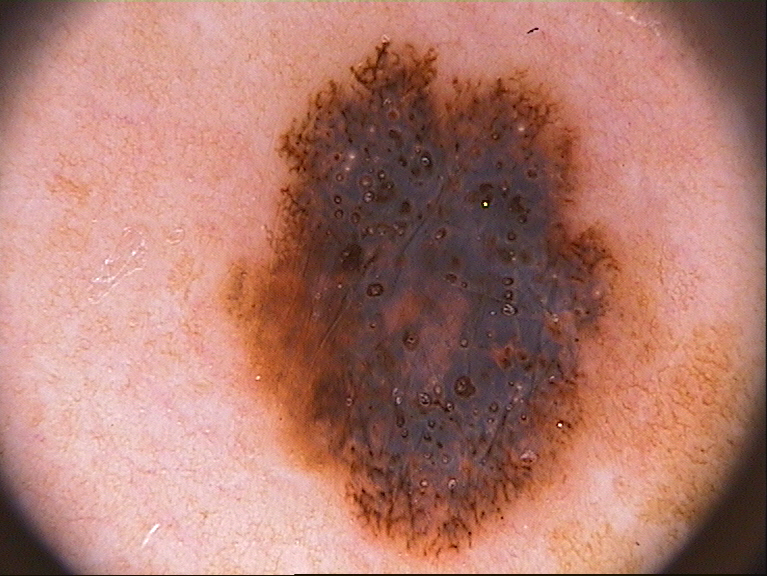Findings:
A dermoscopic close-up of a skin lesion. Dermoscopically, the lesion shows pigment network, globules, streaks, and milia-like cysts. With coordinates (x1, y1, x2, y2), the visible lesion spans [211,32,761,573].
Impression:
The clinical diagnosis was a melanocytic nevus.